The subject is a male aged 30–39 · a close-up photograph · located on the head or neck, arm, back of the torso and front of the torso — 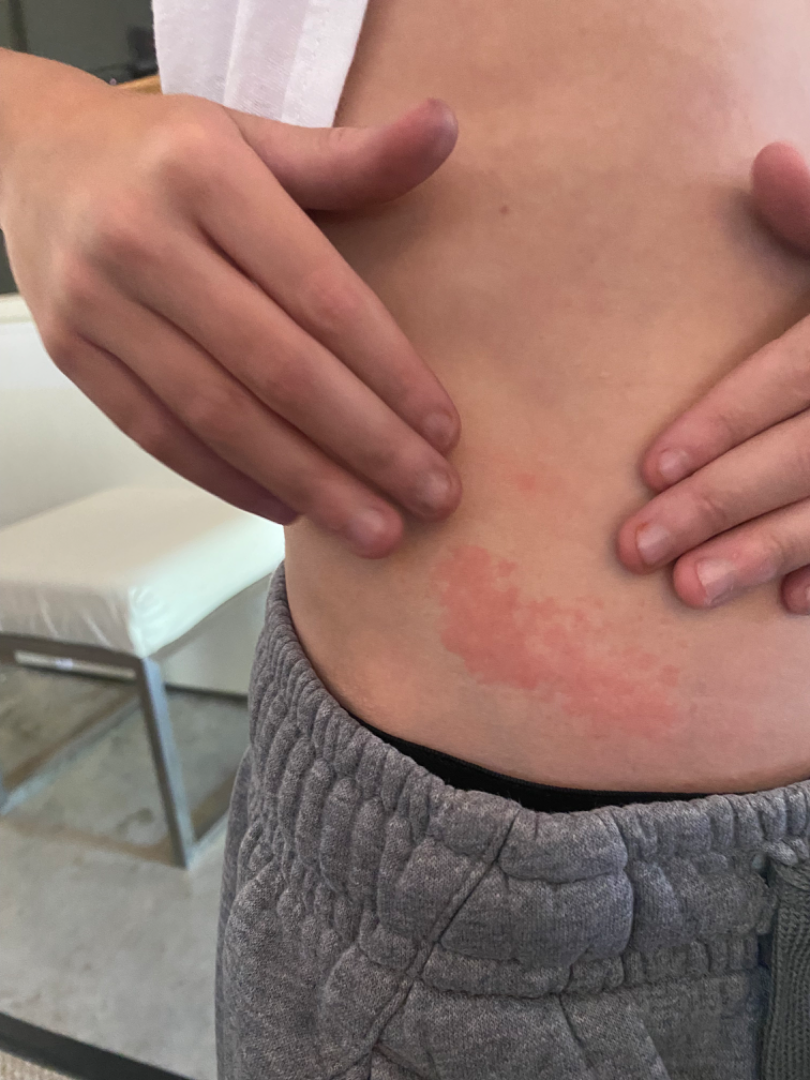Q: What is the dermatologist's impression?
A: reviewed remotely by one dermatologist: most likely Irritant Contact Dermatitis; an alternative is Allergic Contact Dermatitis